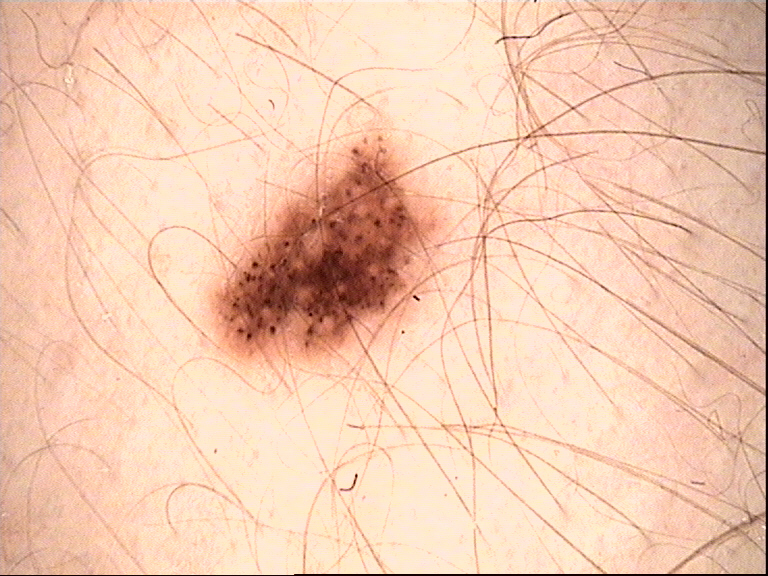The diagnosis was a benign lesion — a dysplastic junctional nevus.